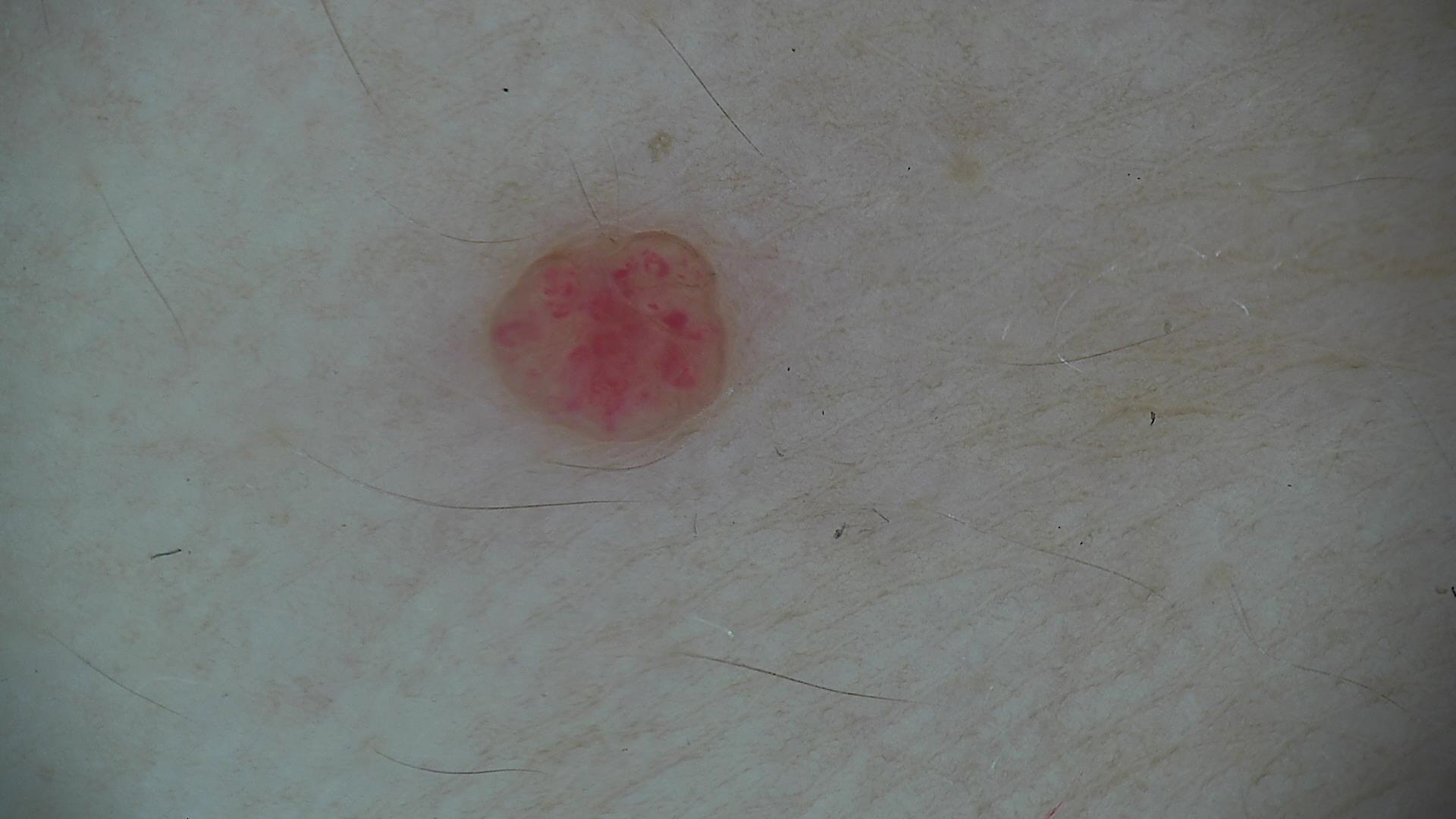A skin lesion imaged with a dermatoscope. Classified as a hemangioma.